This image was taken at an angle, self-categorized by the patient as hair loss, texture is reported as flat, the patient reports bothersome appearance, the lesion involves the arm:
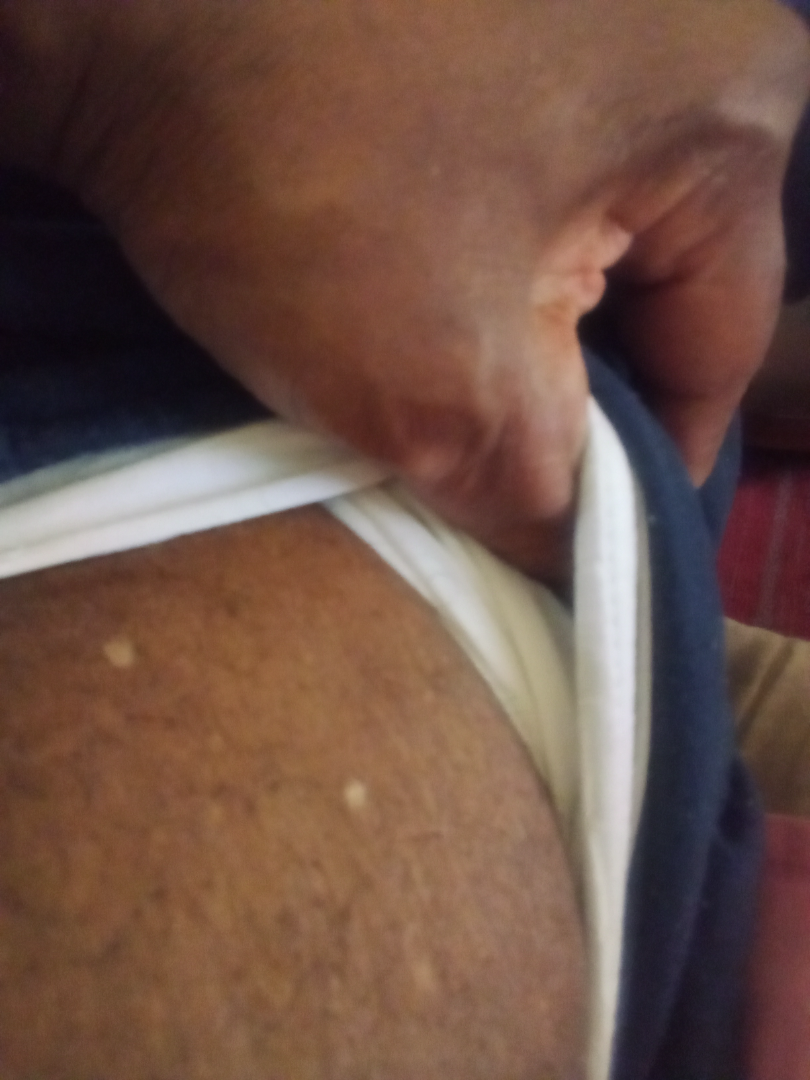Q: What was the assessment?
A: could not be assessed